A clinical photograph of a skin lesion; a female subject in their early 70s:
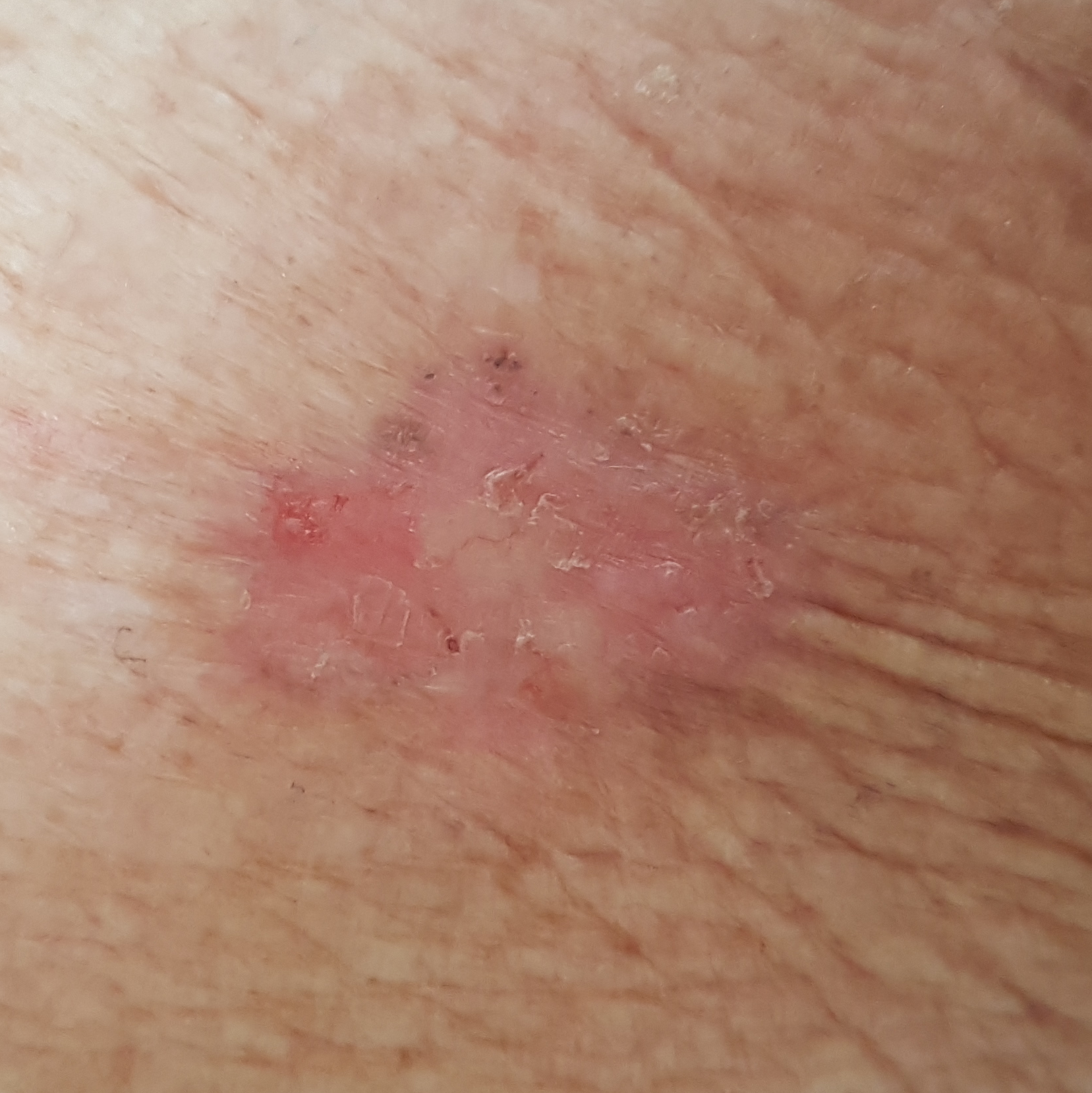The lesion was found on an arm.
By the patient's account, the lesion itches, but is not elevated.
Histopathologically confirmed as a basal cell carcinoma.